Dermoscopy of a skin lesion: 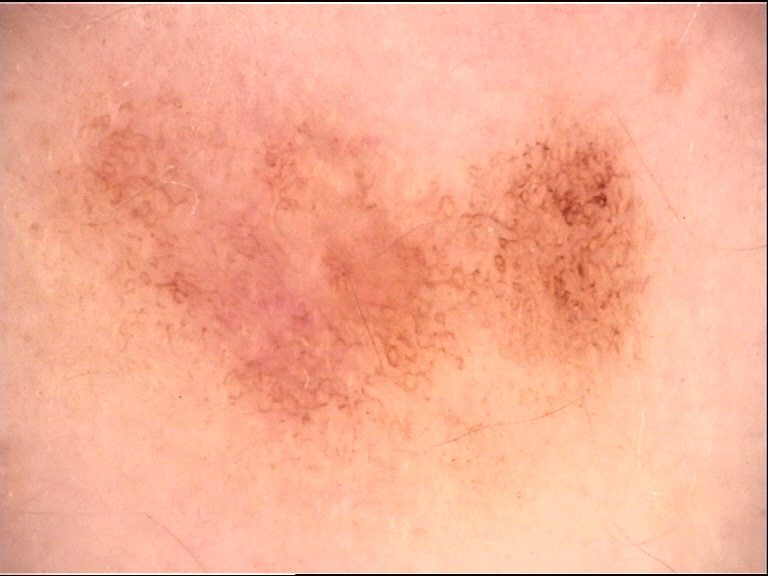Q: What is this lesion?
A: dysplastic junctional nevus (expert consensus)